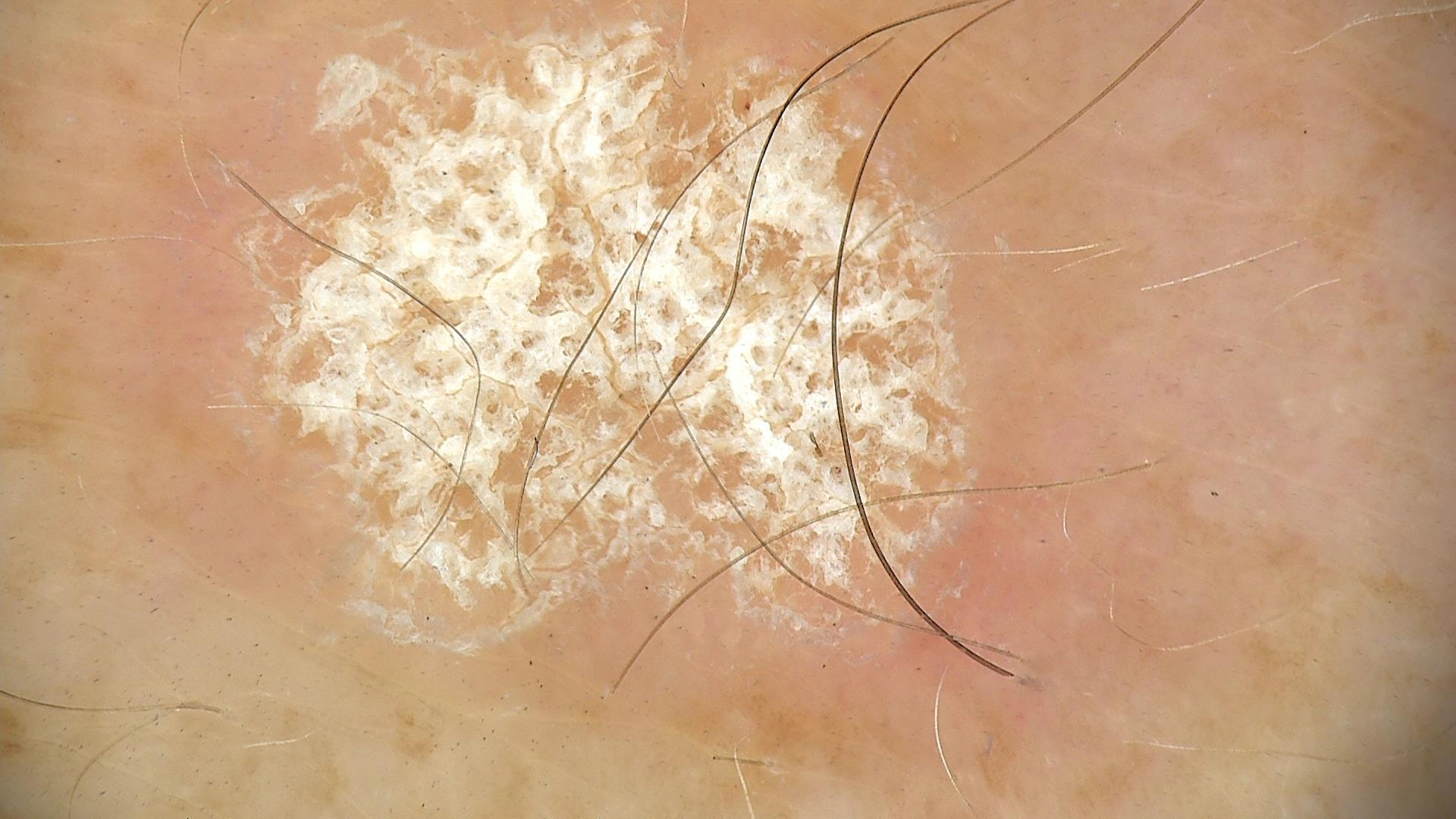Consistent with a seborrheic keratosis.